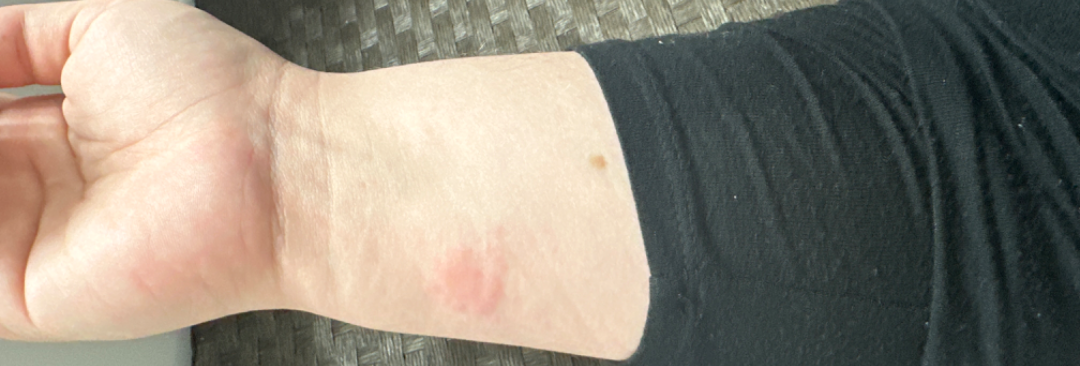The patient indicates the condition has been present for about one day. The affected area is the arm. The patient considered this a rash. Symptoms reported: itching. This image was taken at a distance. Skin tone: Fitzpatrick phototype II; human graders estimated 2 on the MST. On photographic review, the primary impression is Insect Bite.